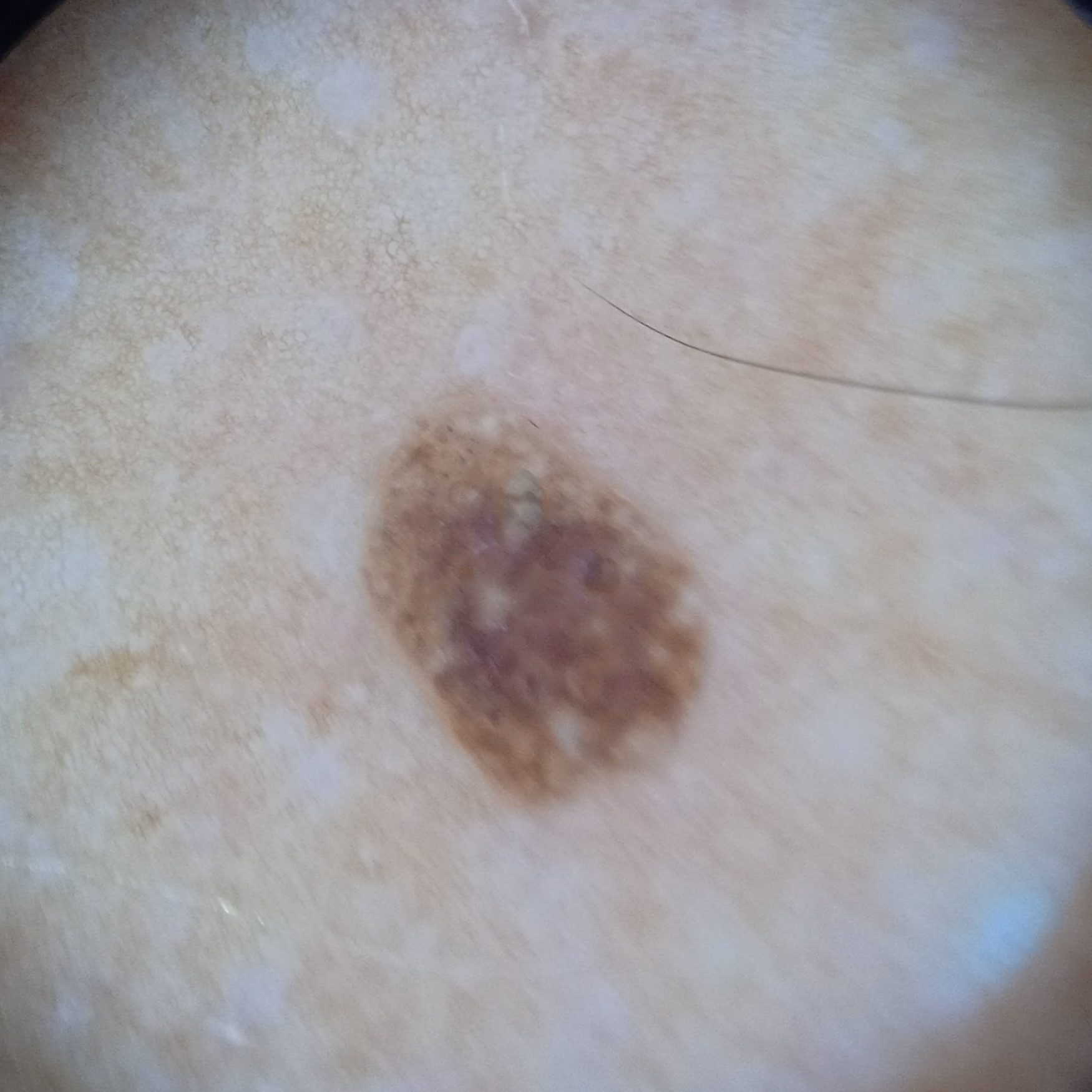clinical context = research study (no referral diagnosis) | sun reaction = skin tans without first burning | risk factors = a personal history of skin cancer, no immunosuppression, no prior organ transplant | diameter = 5.2 mm | diagnostic label = seborrheic keratosis (dermatologist consensus).